A dermoscopic photograph of a skin lesion.
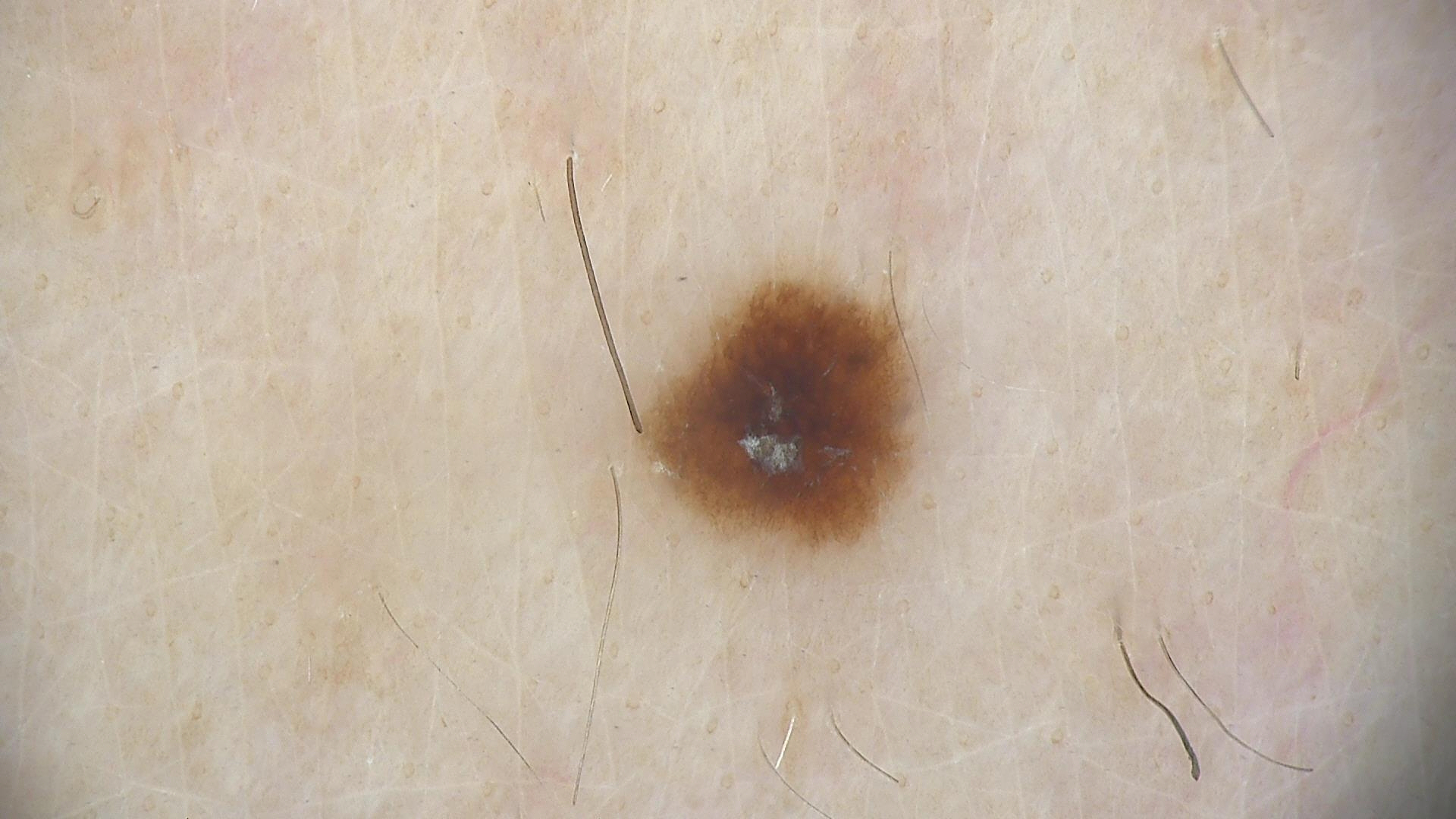Diagnosed as a dysplastic junctional nevus.